The patient described the issue as acne. This is a close-up image. The contributor is 18–29, male. The patient indicates the condition has been present for about one day. The lesion is described as raised or bumpy. No constitutional symptoms were reported. The arm, leg, head or neck and back of the hand are involved — 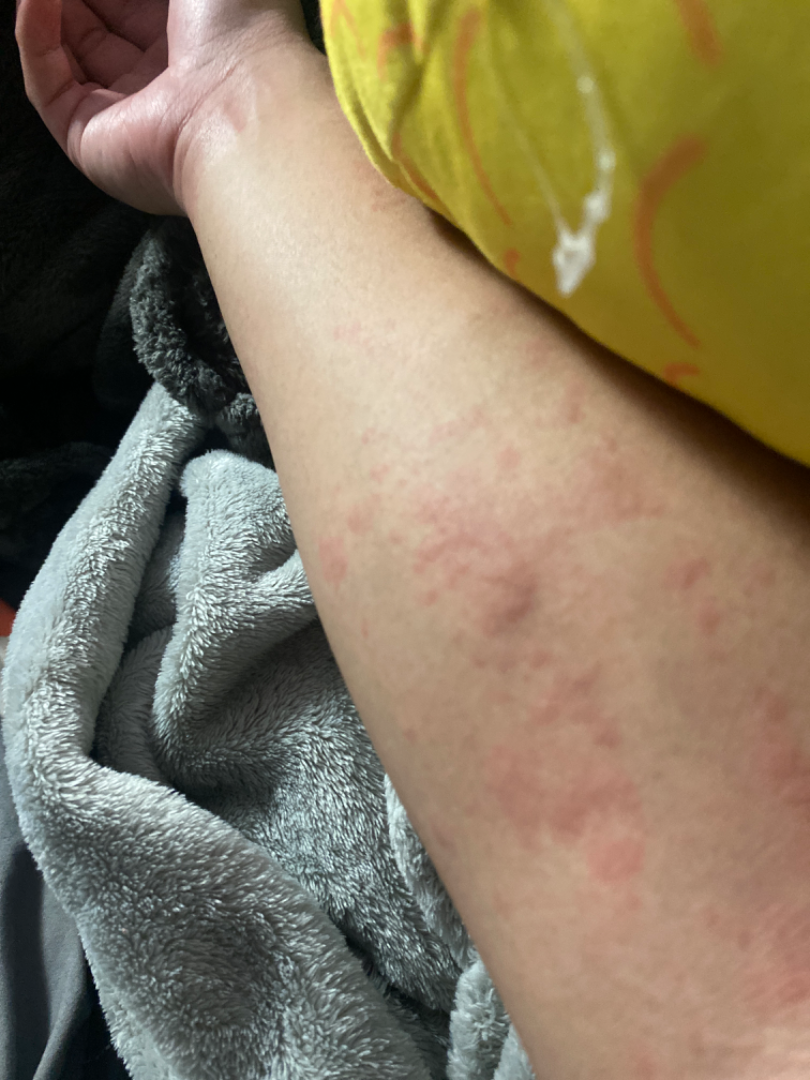| key | value |
|---|---|
| clinical impression | a single dermatologist reviewed the case: consistent with Urticaria |